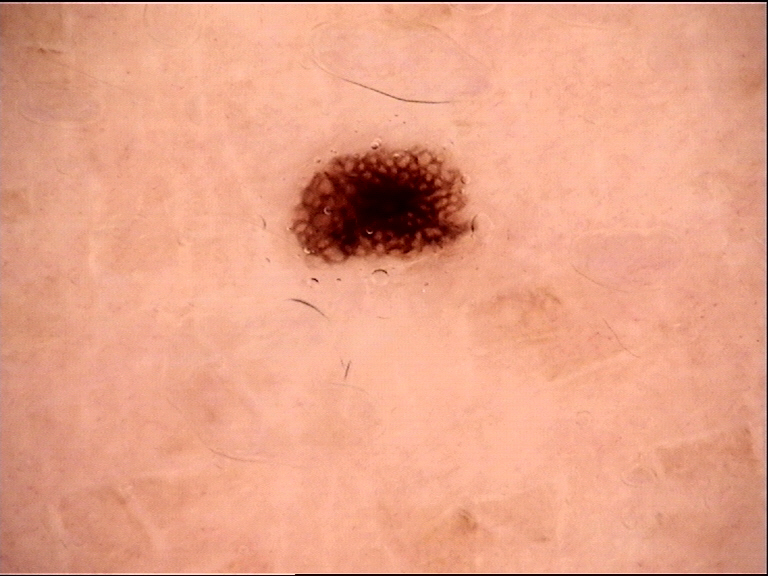diagnostic label=dysplastic junctional nevus (expert consensus).